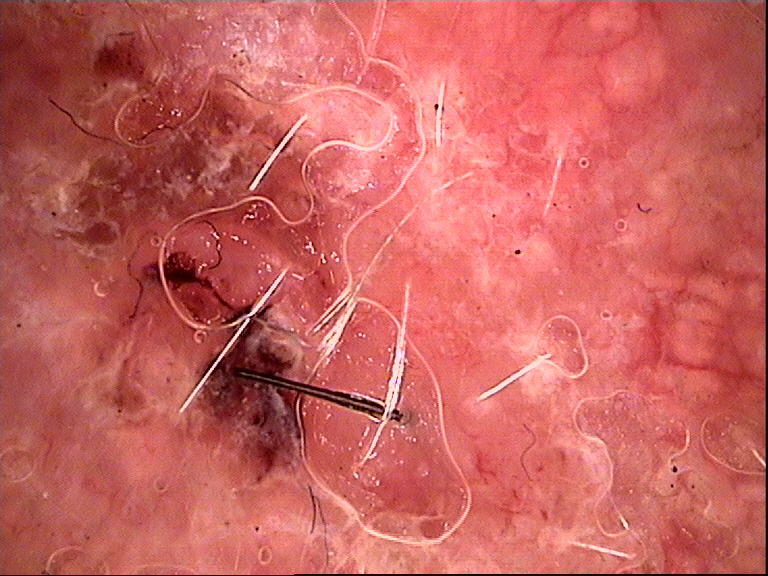{
  "diagnosis": {
    "name": "basal cell carcinoma",
    "code": "bcc",
    "malignancy": "malignant",
    "super_class": "non-melanocytic",
    "confirmation": "histopathology"
  }
}